Female patient, age 30–39. The arm is involved. The photograph was taken at a distance: 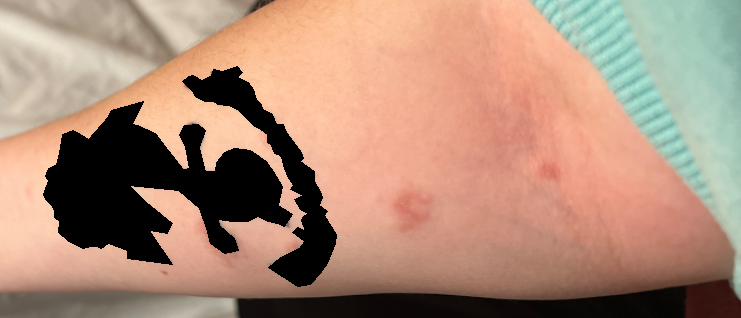| field | value |
|---|---|
| clinical impression | reviewed remotely by three dermatologists: Cutaneous sarcoidosis and Allergic Contact Dermatitis were each considered, in no particular order |